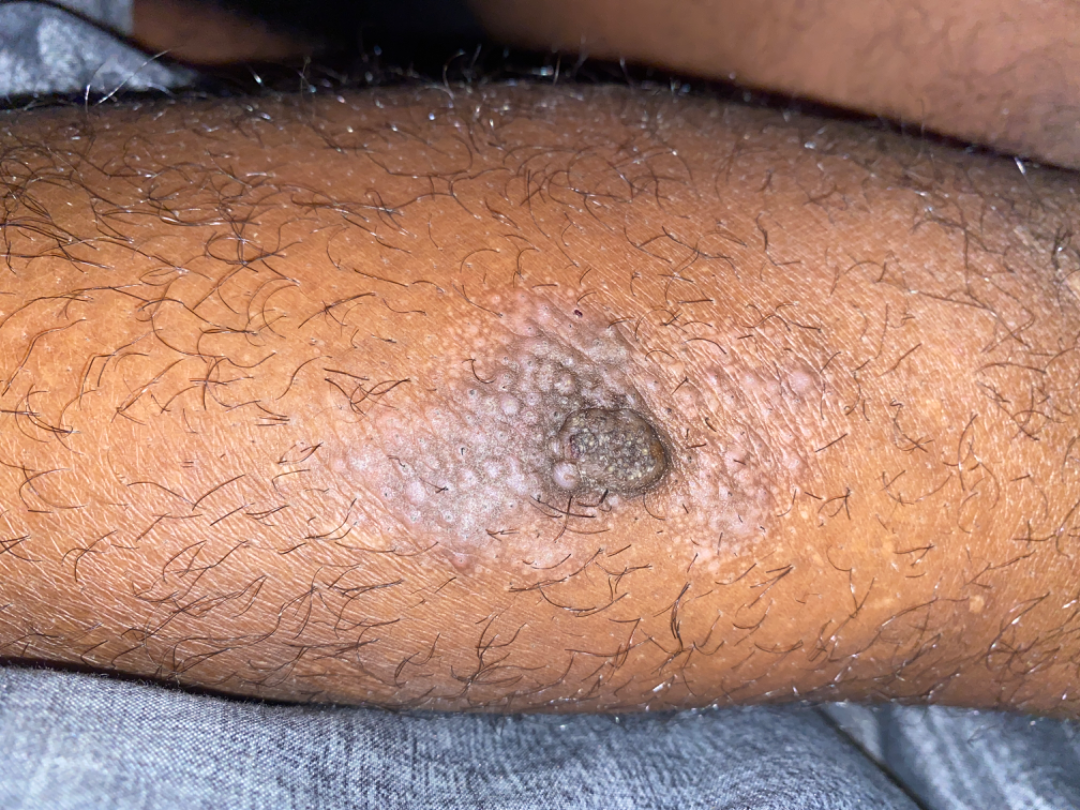diagnostic considerations: Prurigo nodularis and Lichen Simplex Chronicus were considered with similar weight; lower on the differential is Lichen planus/lichenoid eruption.